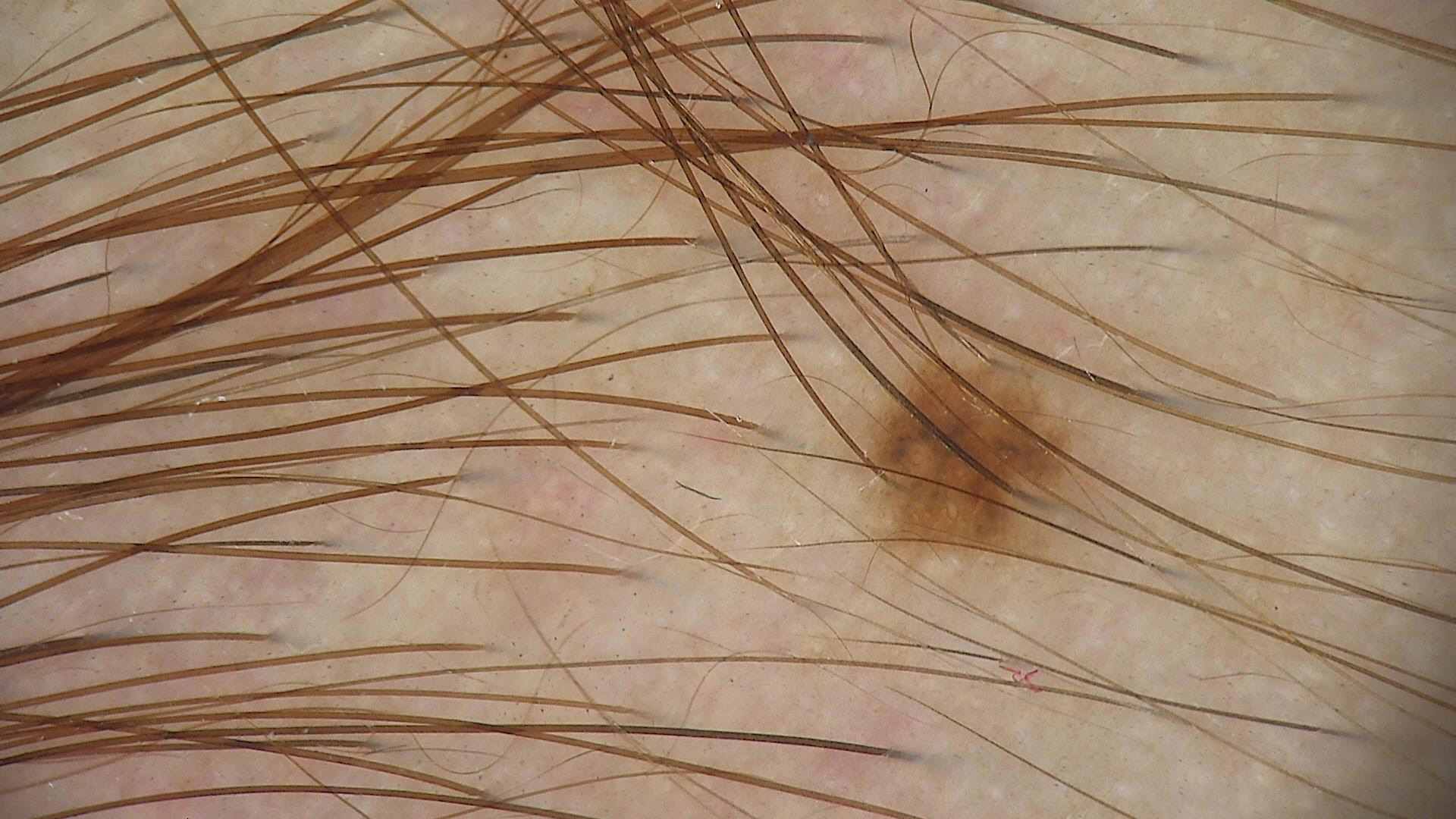label=dysplastic compound nevus (expert consensus)